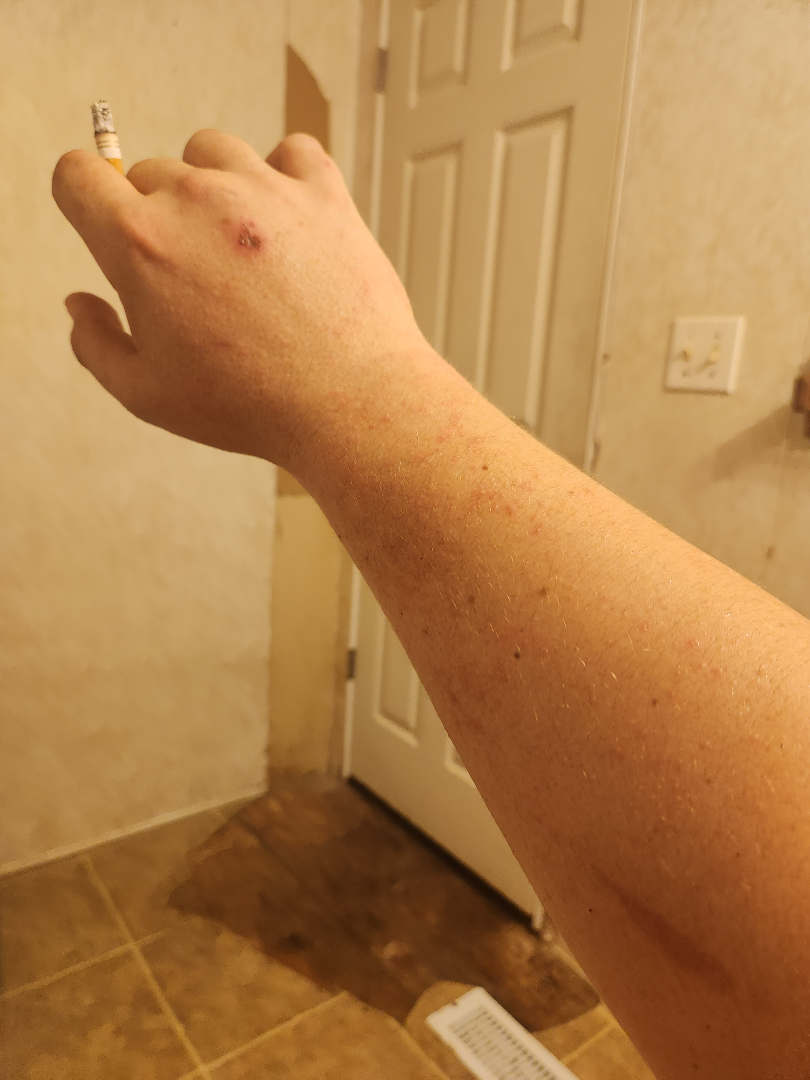<dermatology_case>
  <differential>
    <Allergic Contact Dermatitis>0.54</Allergic Contact Dermatitis>
    <Drug Rash>0.23</Drug Rash>
    <Viral Exanthem>0.23</Viral Exanthem>
  </differential>
</dermatology_case>